A female subject, aged approximately 70. A dermoscopy image of a single skin lesion.
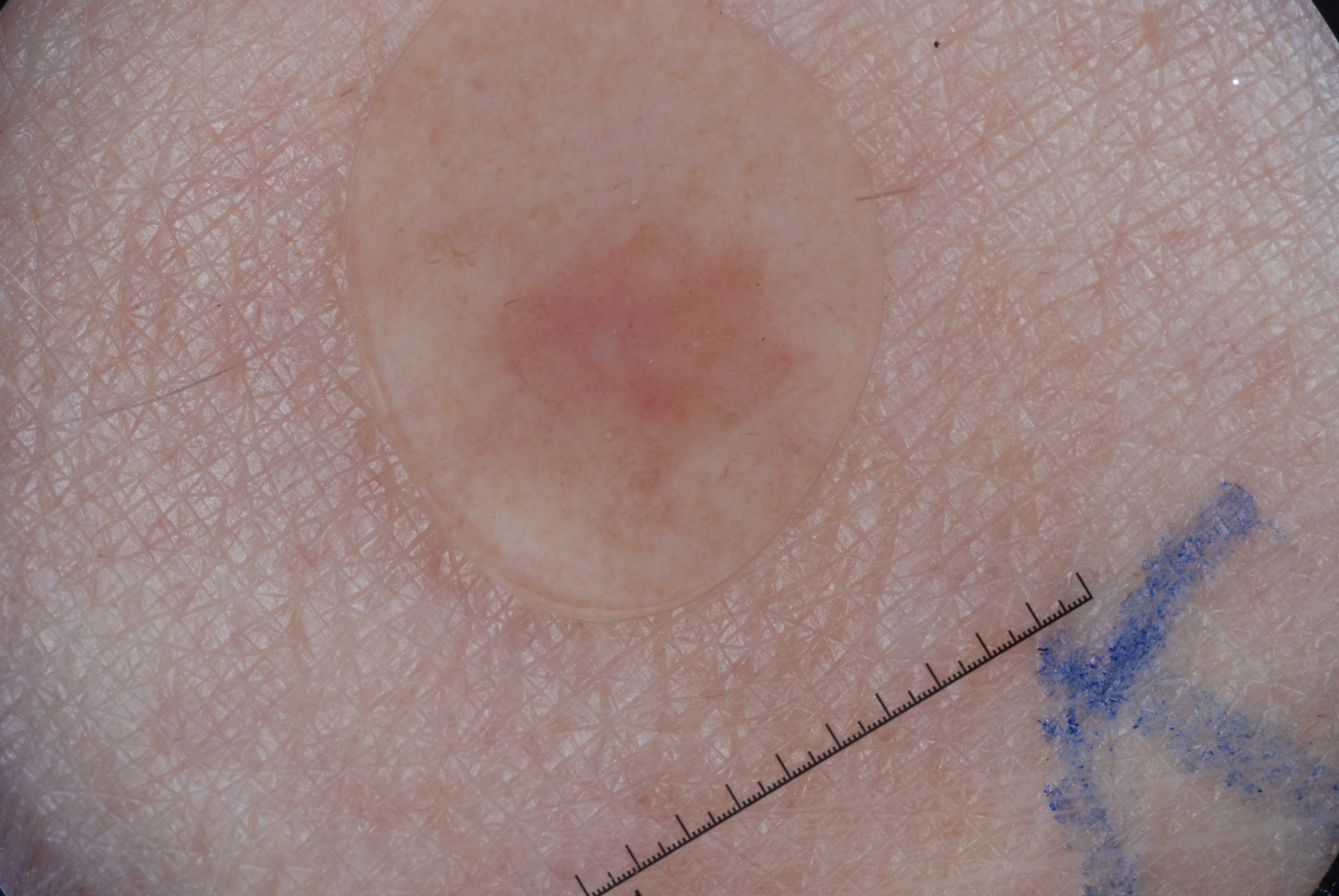lesion size = moderate; absent dermoscopic features = pigment network, negative network, streaks, and milia-like cysts; lesion location = left=473, top=172, right=830, bottom=571; diagnostic label = a seborrheic keratosis.